A dermoscopic photograph of a skin lesion.
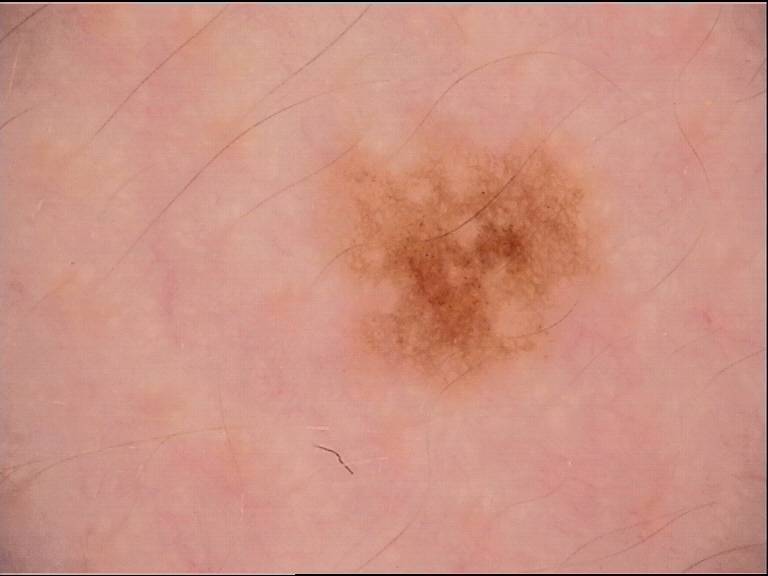Impression:
Consistent with a banal lesion — a junctional nevus.